Recorded as Fitzpatrick phototype II — 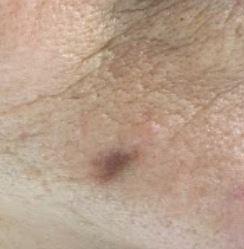The lesion involves the head or neck. Histopathology confirmed a tumor of follicular differentiation — a basal cell carcinoma.